A clinical photograph showing a skin lesion — 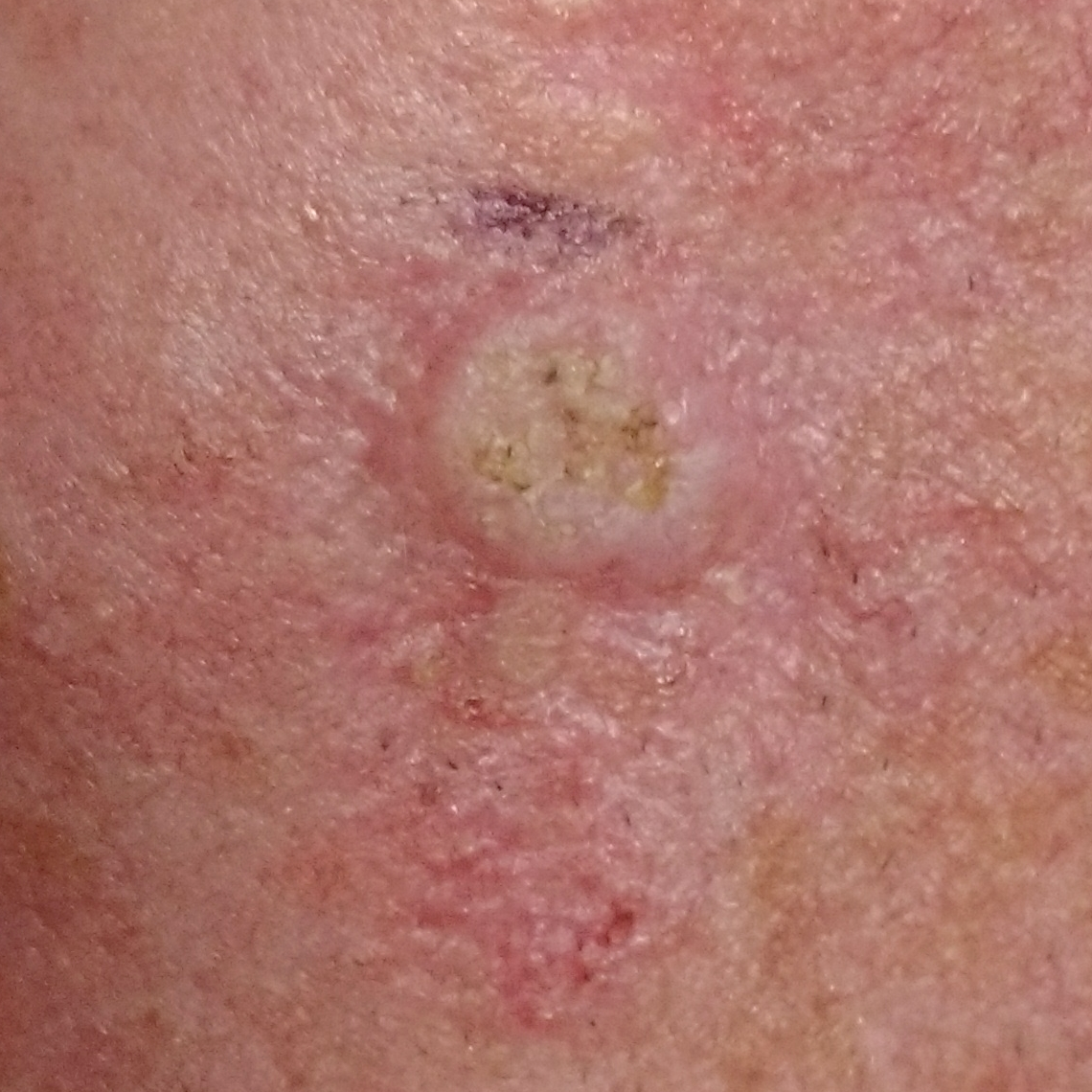<case>
<lesion_location>the face</lesion_location>
<symptoms>
<present>itching, elevation</present>
<absent>pain</absent>
</symptoms>
<diagnosis>
<name>squamous cell carcinoma</name>
<code>SCC</code>
<malignancy>malignant</malignancy>
<confirmation>histopathology</confirmation>
</diagnosis>
</case>